The lesion is described as raised or bumpy; the photograph was taken at an angle; no constitutional symptoms were reported; the patient described the issue as a rash; the patient reports itching; the back of the torso, arm and leg are involved.
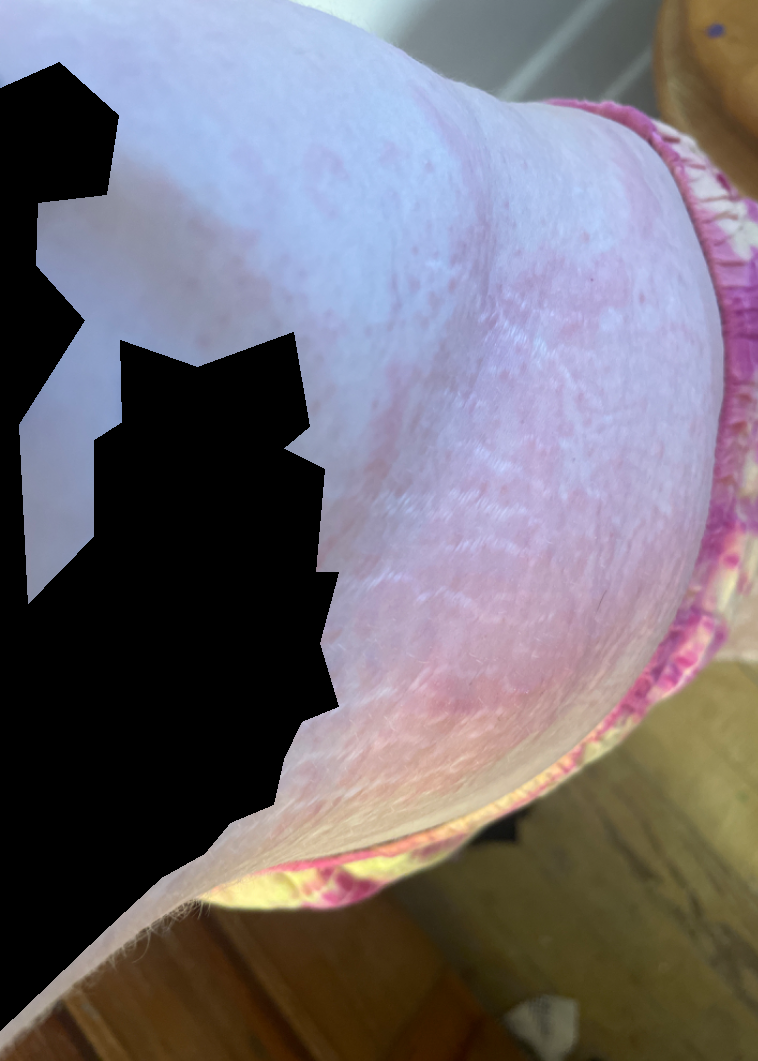Findings: On dermatologist assessment of the image, the differential is split between Urticaria and Drug Rash.